Dermoscopy of a skin lesion: 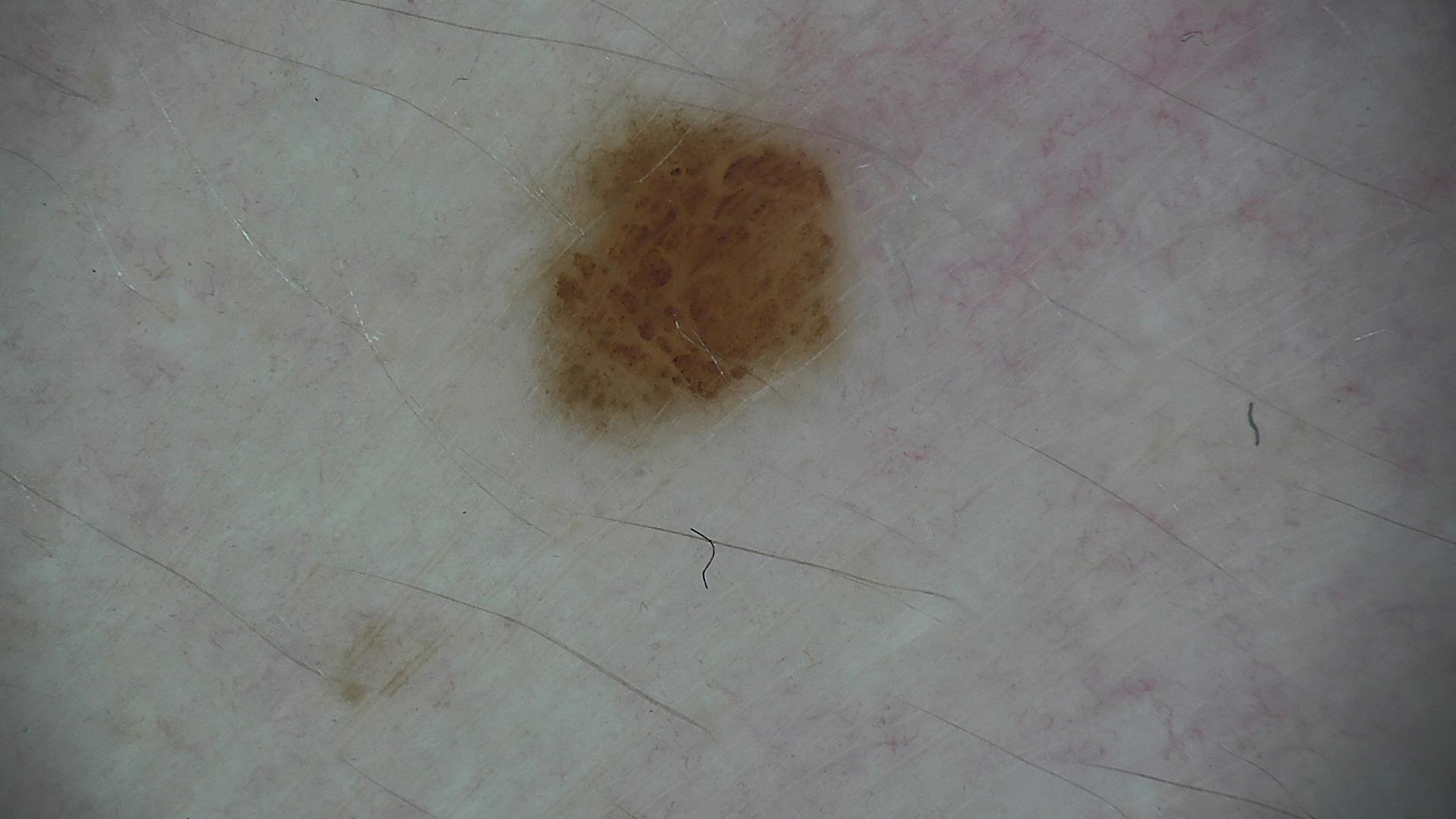The morphology is that of a banal lesion. Consistent with a compound nevus.